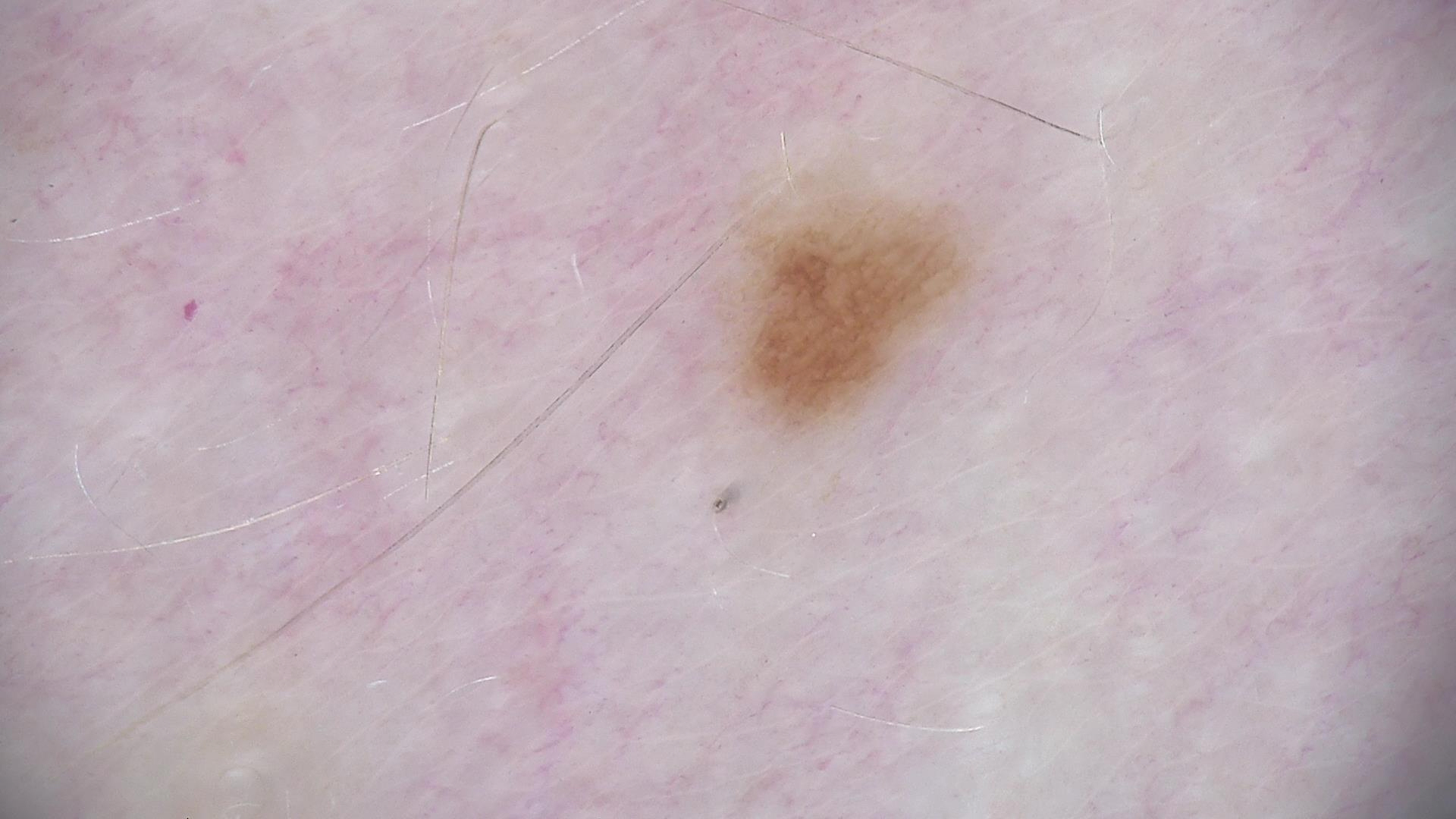{"image": "dermoscopy", "diagnosis": {"name": "dysplastic junctional nevus", "code": "jd", "malignancy": "benign", "super_class": "melanocytic", "confirmation": "expert consensus"}}